The leg and front of the torso are involved, close-up view, the patient is a female aged 18–29.
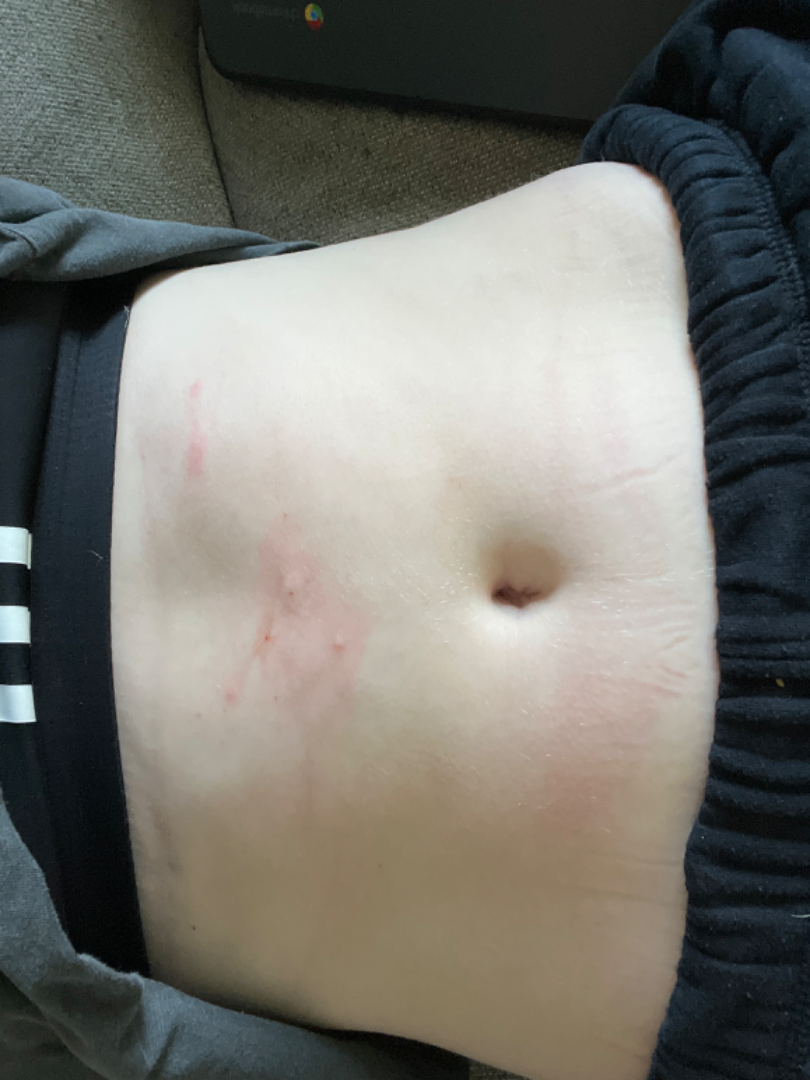Background:
Skin tone: Fitzpatrick III; non-clinician graders estimated Monk skin tone scale 2. Texture is reported as fluid-filled and raised or bumpy. The patient considered this a rash. Reported duration is less than one week.
Findings:
On photographic review by a dermatologist, in keeping with Allergic Contact Dermatitis.